Symptoms reported: burning. Located on the leg. Present for less than one week. Fitzpatrick phototype III. This image was taken at an angle. The lesion is described as fluid-filled and raised or bumpy.
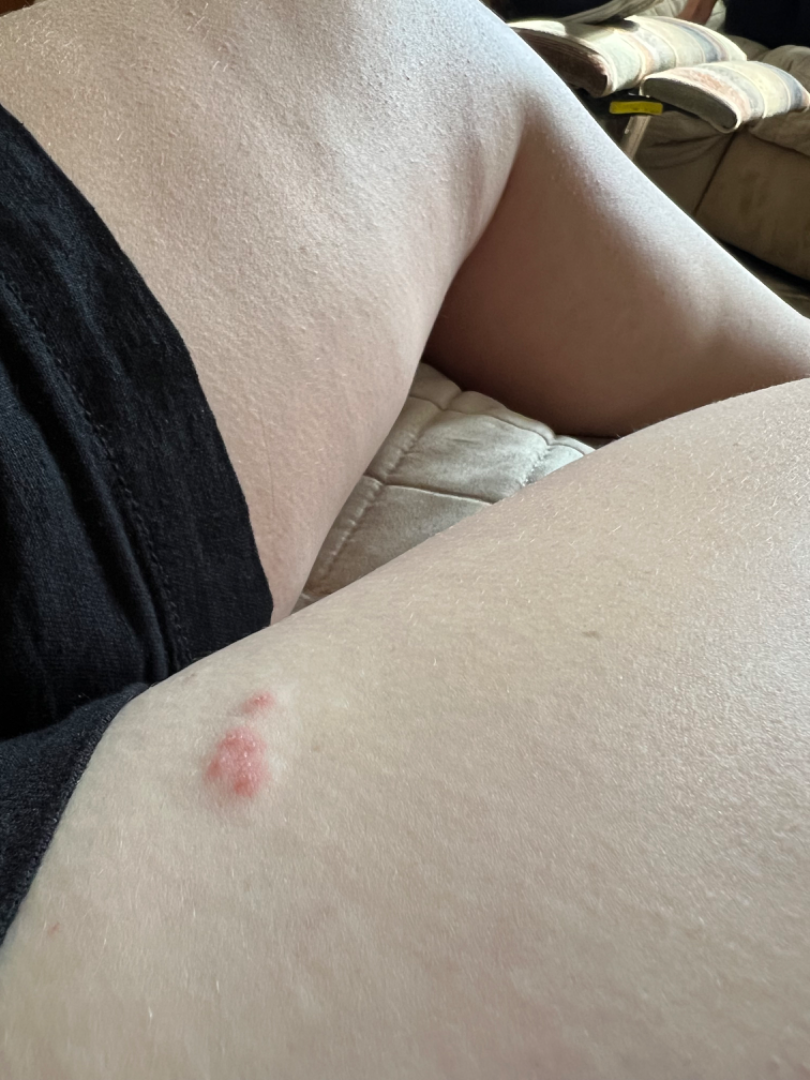Consistent with Herpes Simplex.